A dermoscopy image of a skin lesion. Collected as part of a research study, without a referral diagnosis. A male patient aged 66. Few moles overall by the patient's own estimate. On a questionnaire the patient reported a prior organ transplant, no sunbed use, and no family history of skin cancer. The patient says their skin reddens with sun exposure.
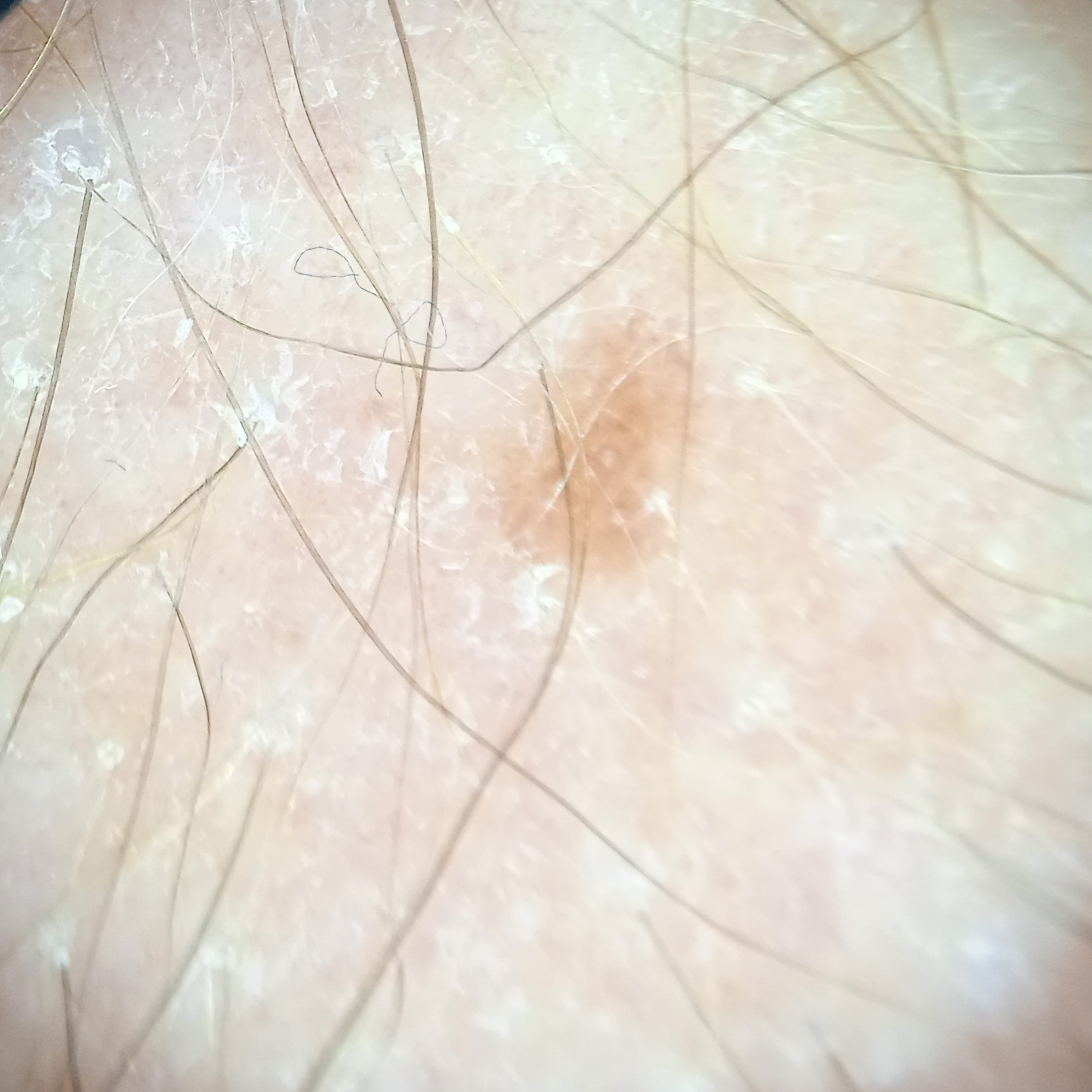Case:
- location — an arm
- lesion size — 3.4 mm
- diagnosis — melanocytic nevus (dermatologist consensus)